The photo was captured at an angle; the leg is involved; the subject is a male aged 30–39: 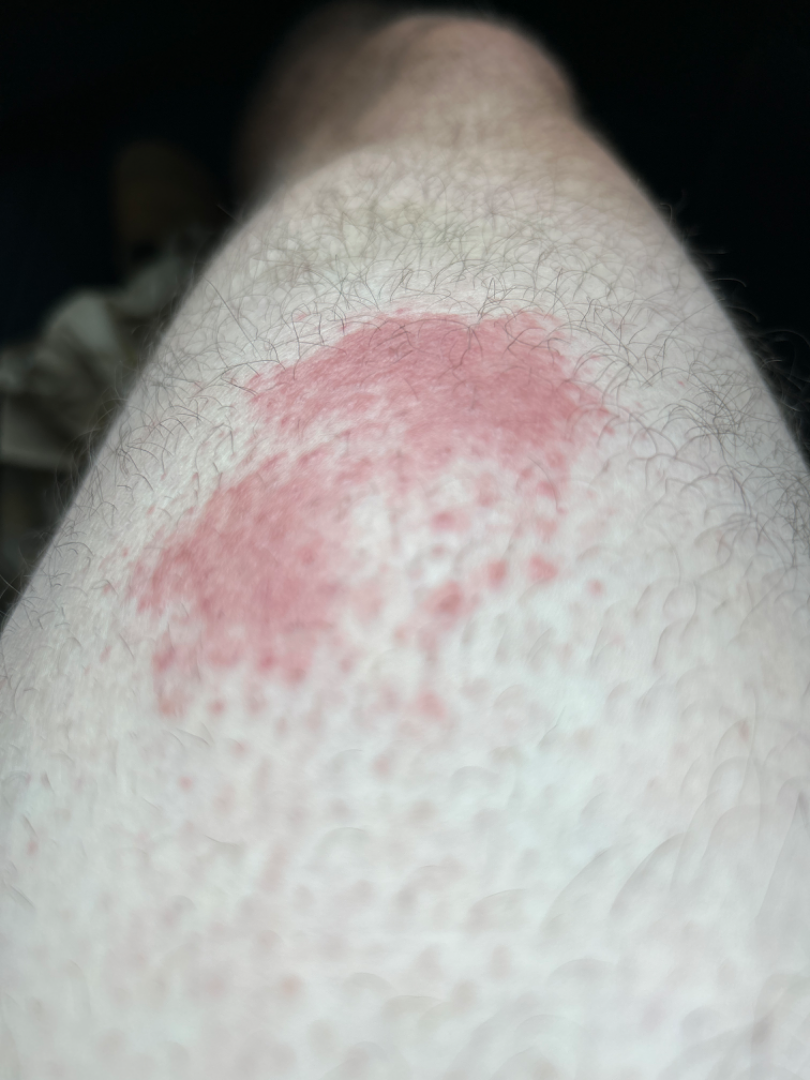The skin findings could not be characterized from the image.
The patient reports bothersome appearance.
The lesion is described as raised or bumpy.
The patient considered this a rash.